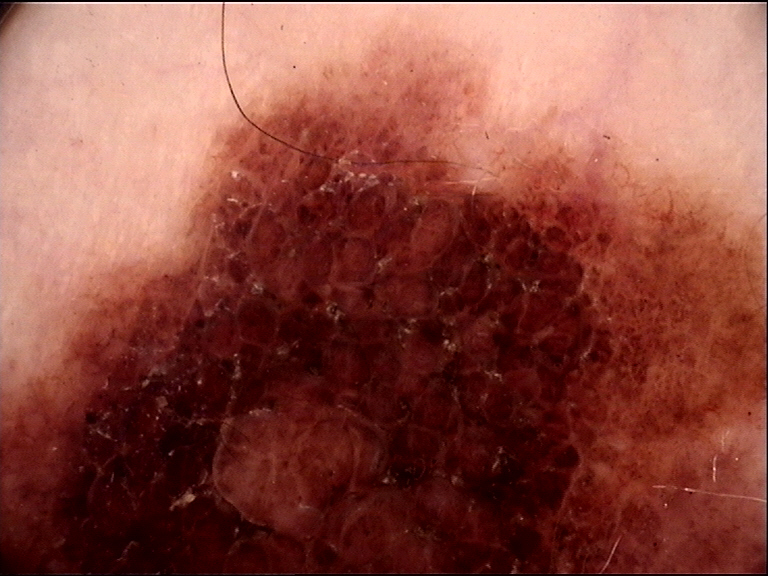Findings: A dermatoscopic image of a skin lesion. Conclusion: Consistent with a dysplastic compound nevus.